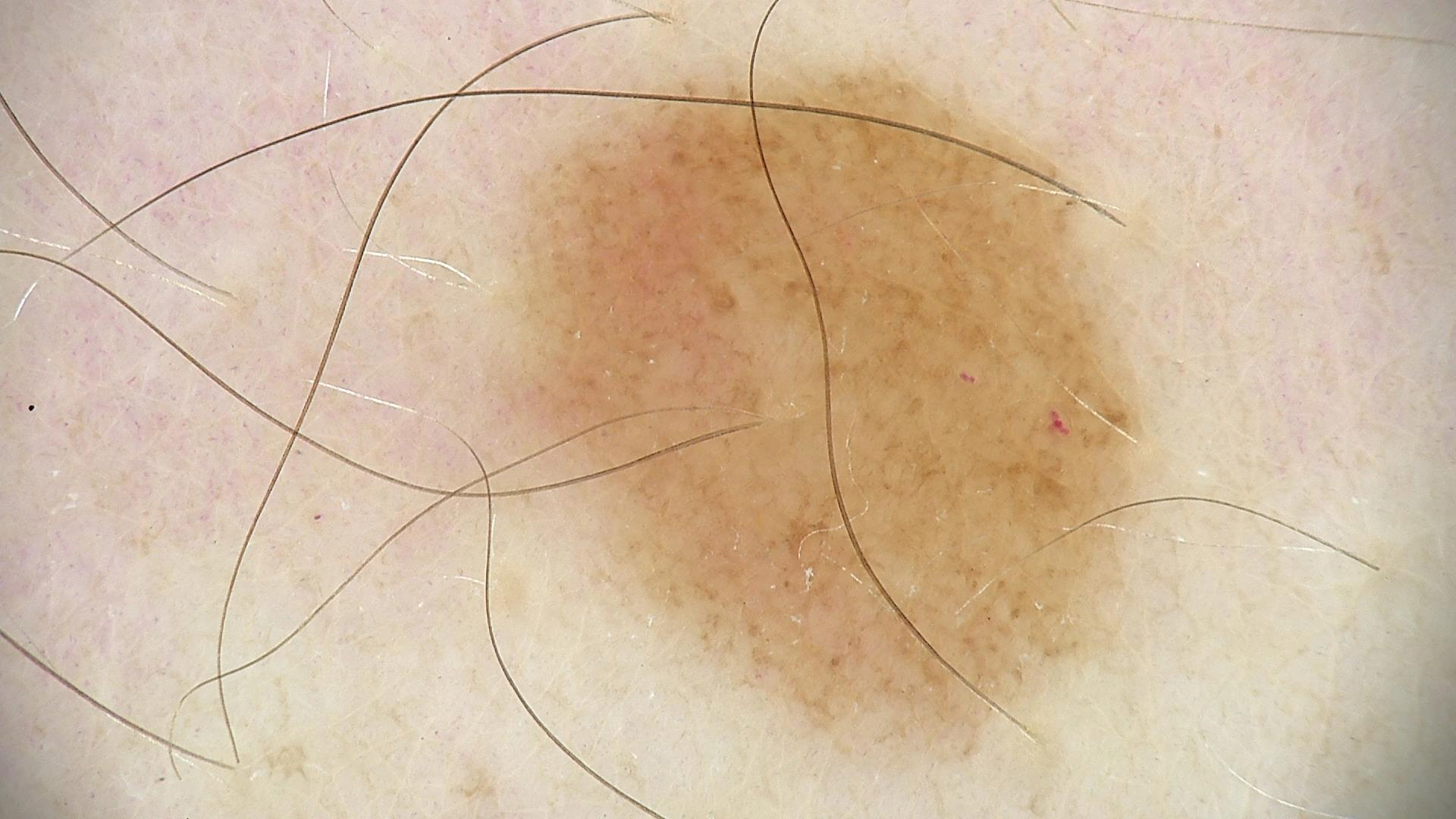The diagnostic label was a compound nevus.